The subject is a male aged 50–59, located on the leg, the photograph is a close-up of the affected area: 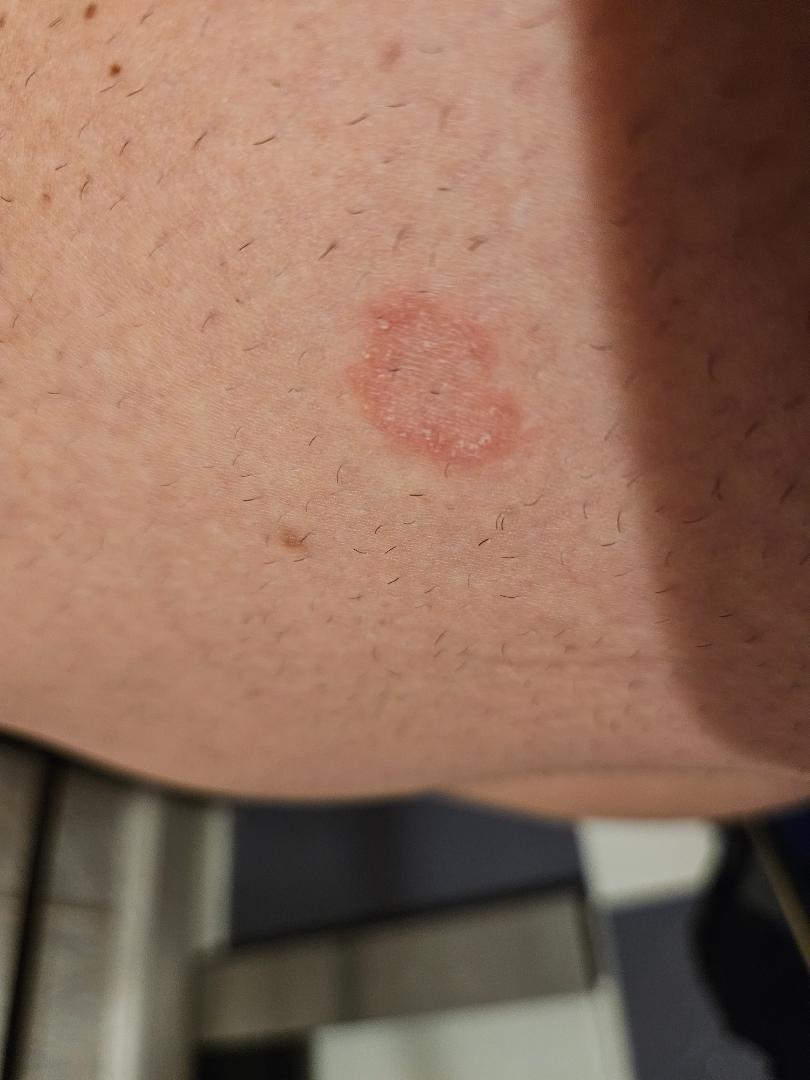Patient information: The contributor reports the lesion is flat. Symptoms reported: itching. Present for one to four weeks. Review: Porokeratosis, Tinea and Eczema were each considered, in no particular order.